The contributor is 30–39, female; the photograph is a close-up of the affected area: 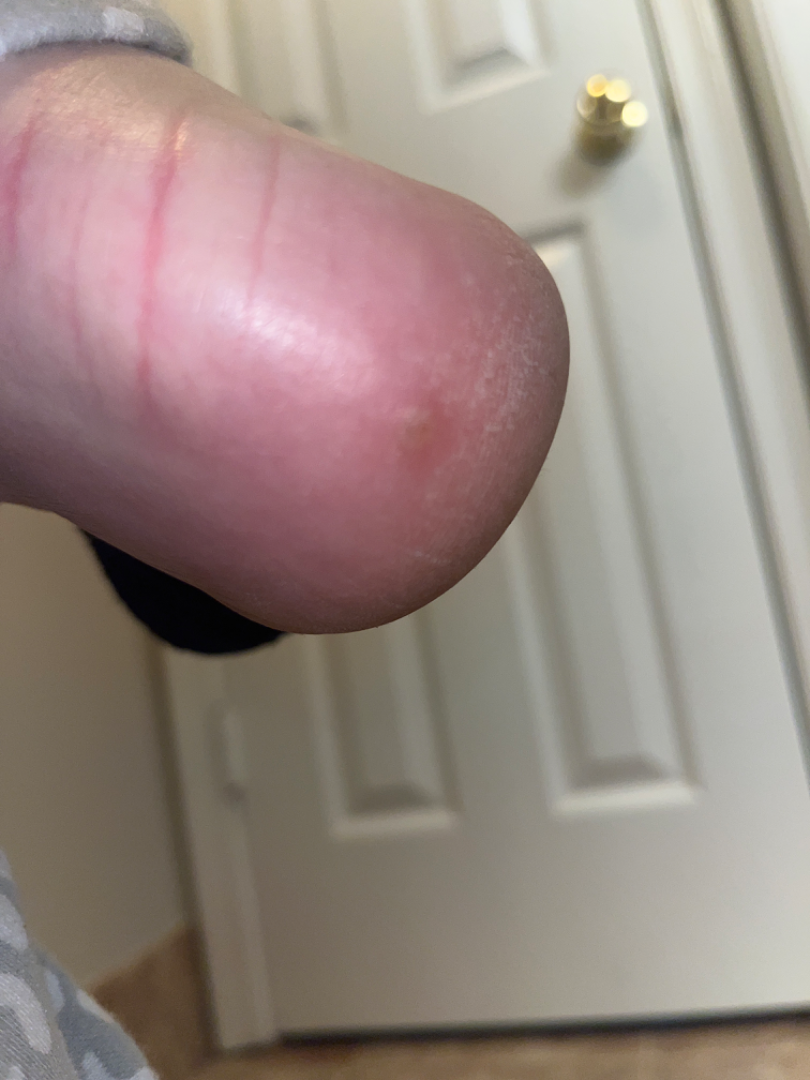No differential diagnosis could be assigned on photographic review.